A male patient about 55 years old. Dermoscopy of a skin lesion — 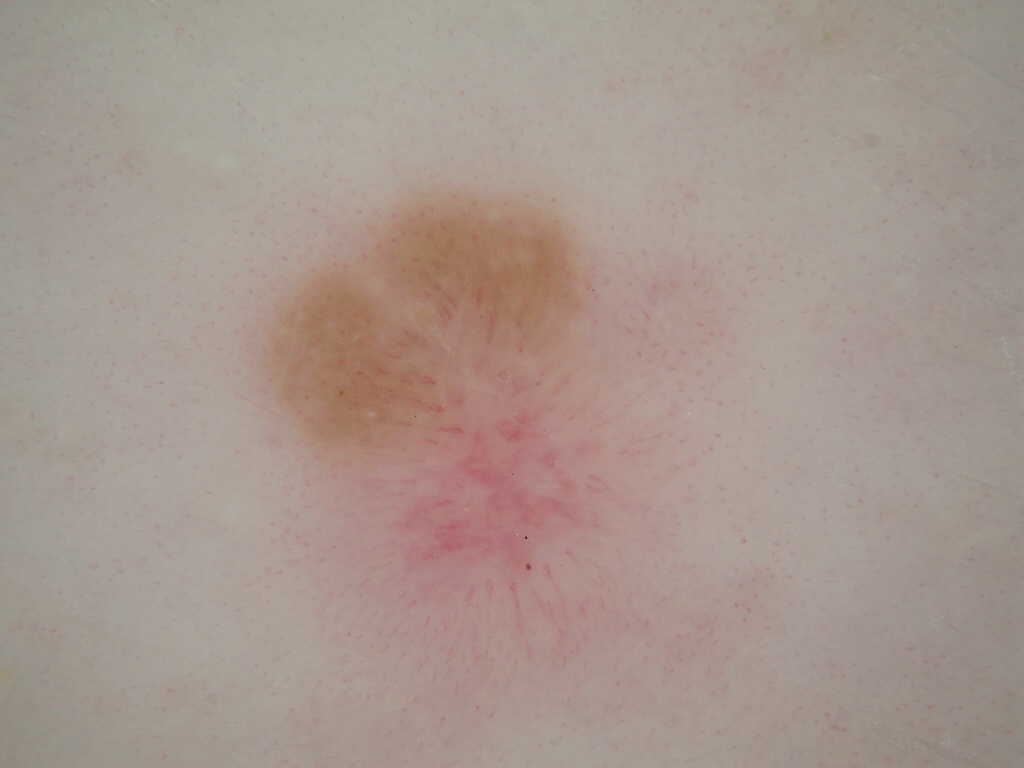Summary:
With coordinates (x1, y1, x2, y2), the lesion is bounded by [235,163,795,744]. Dermoscopy demonstrates no negative network, streaks, milia-like cysts, globules, or pigment network.
Impression:
The diagnostic assessment was a melanocytic nevus.